Dermoscopy of a skin lesion:
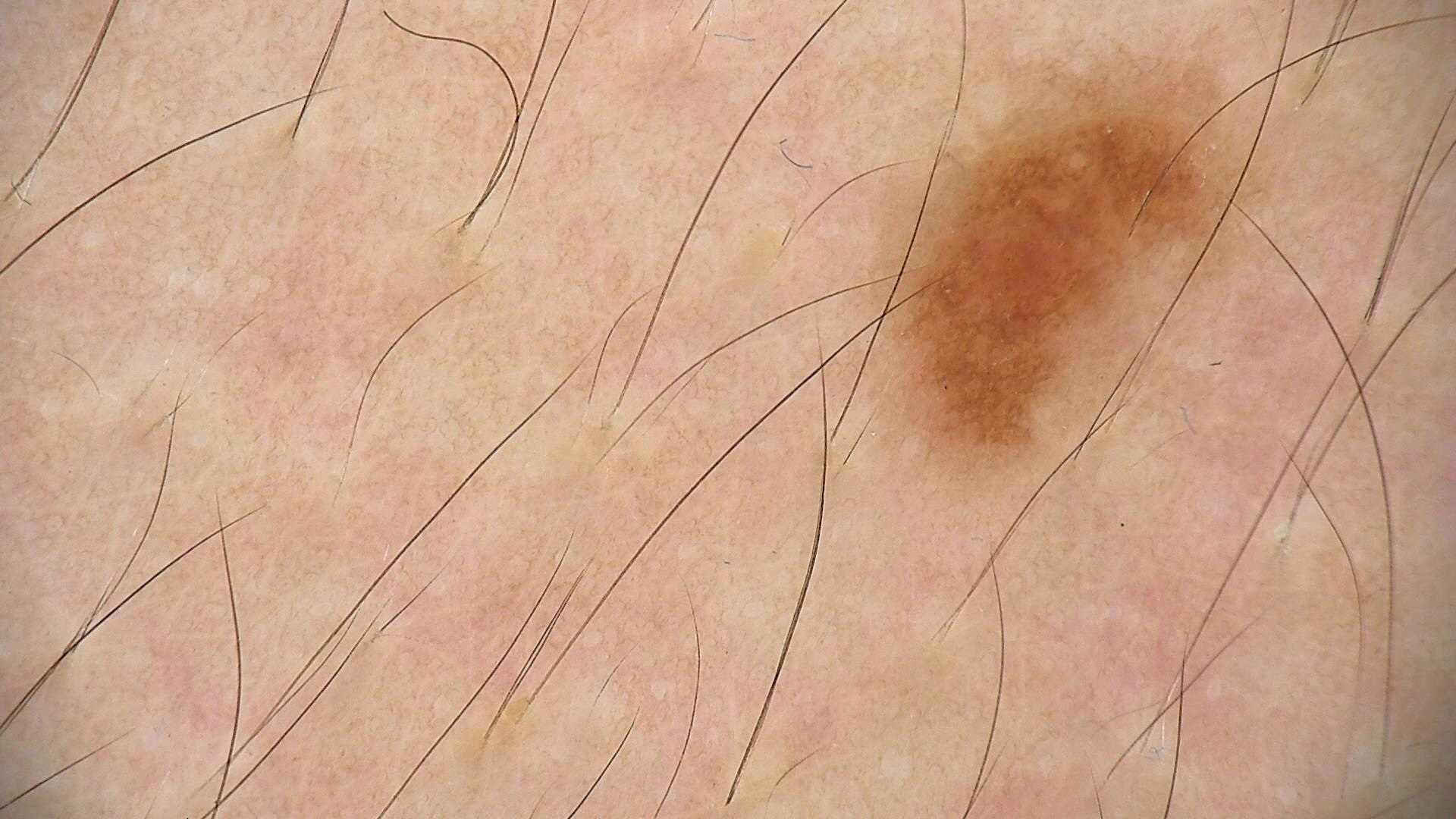diagnostic label — dysplastic junctional nevus (expert consensus).